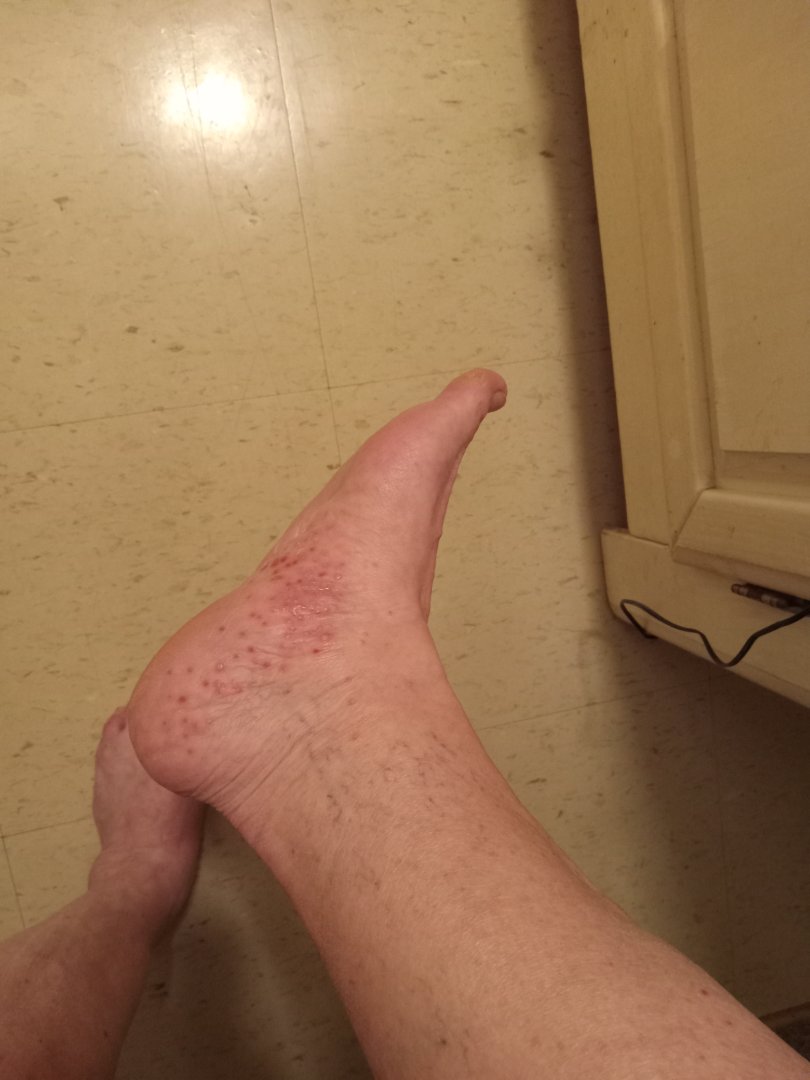Impression: On dermatologist assessment of the image: the favored diagnosis is Eczema.